A dermatoscopic image of a skin lesion.
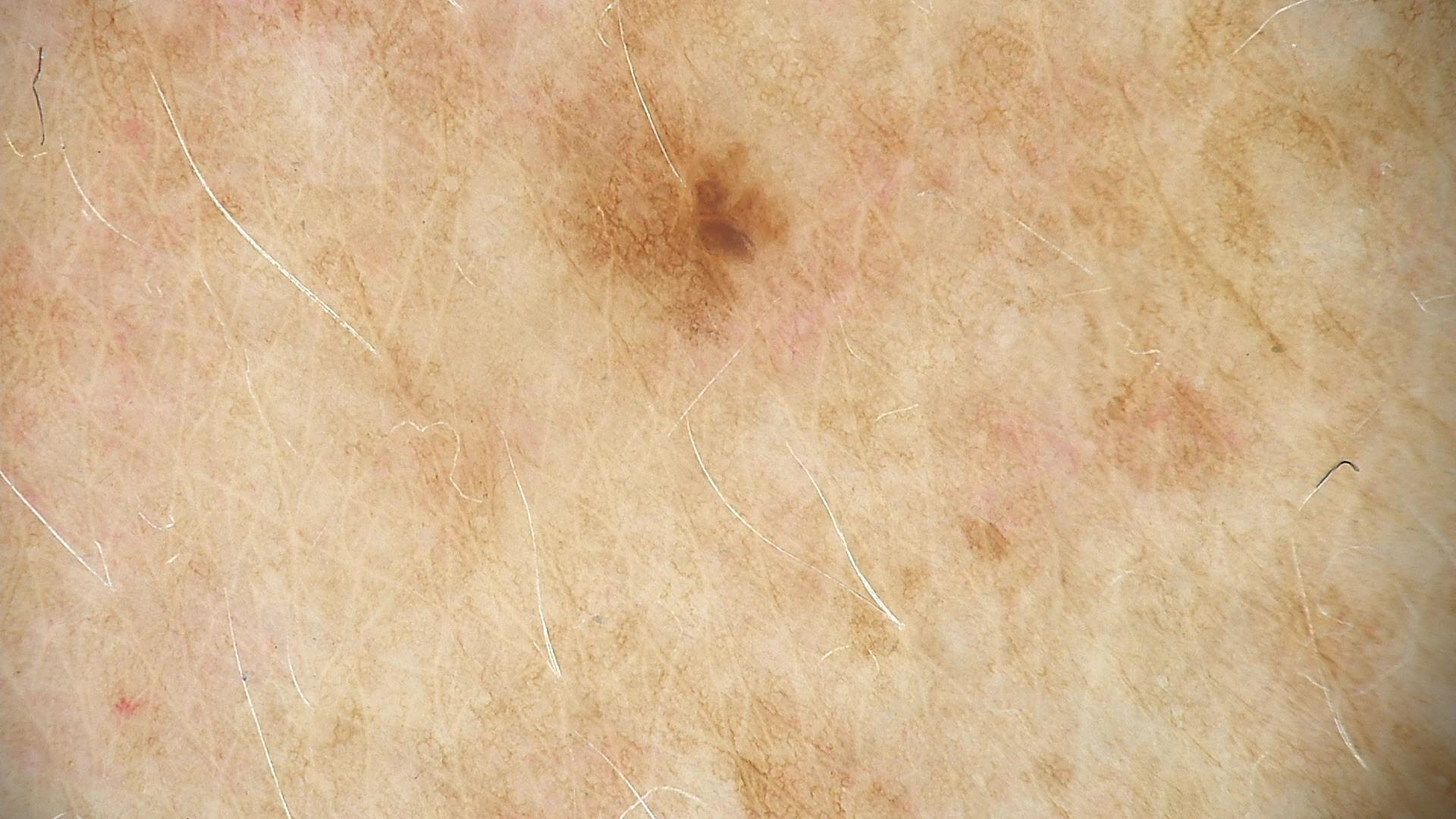Case:
– diagnostic label · seborrheic keratosis (expert consensus)